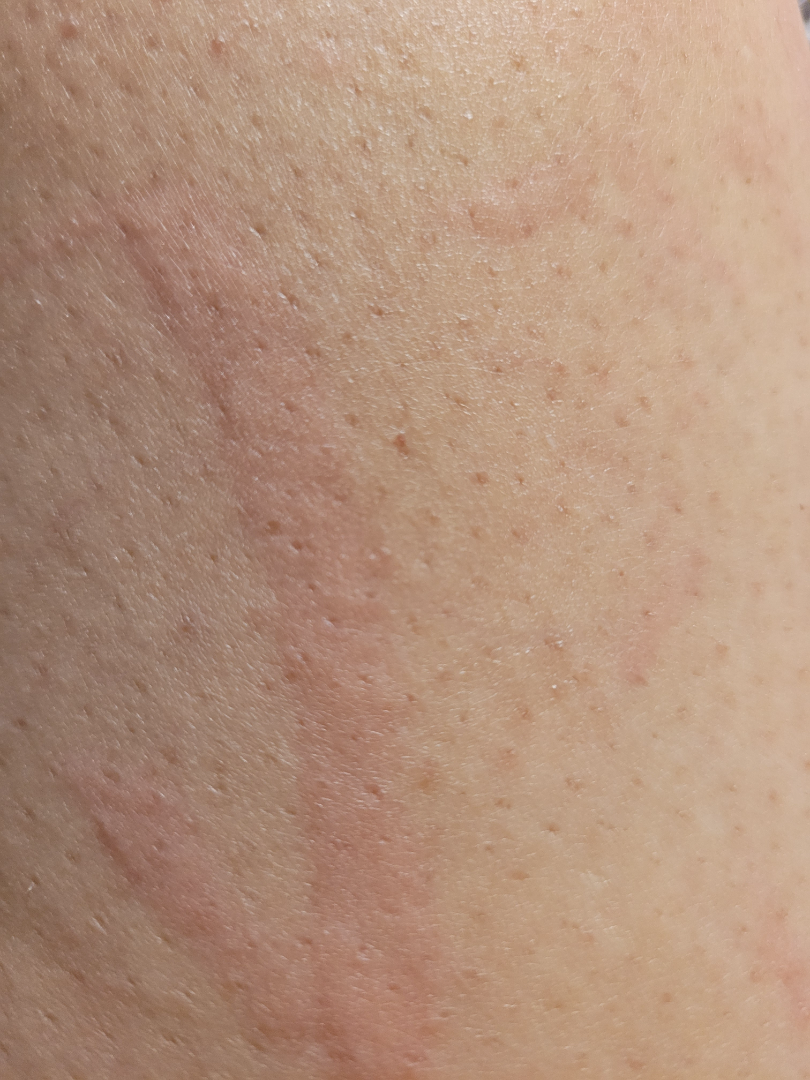{"shot_type": "close-up", "differential": {"leading": ["Urticaria"]}}